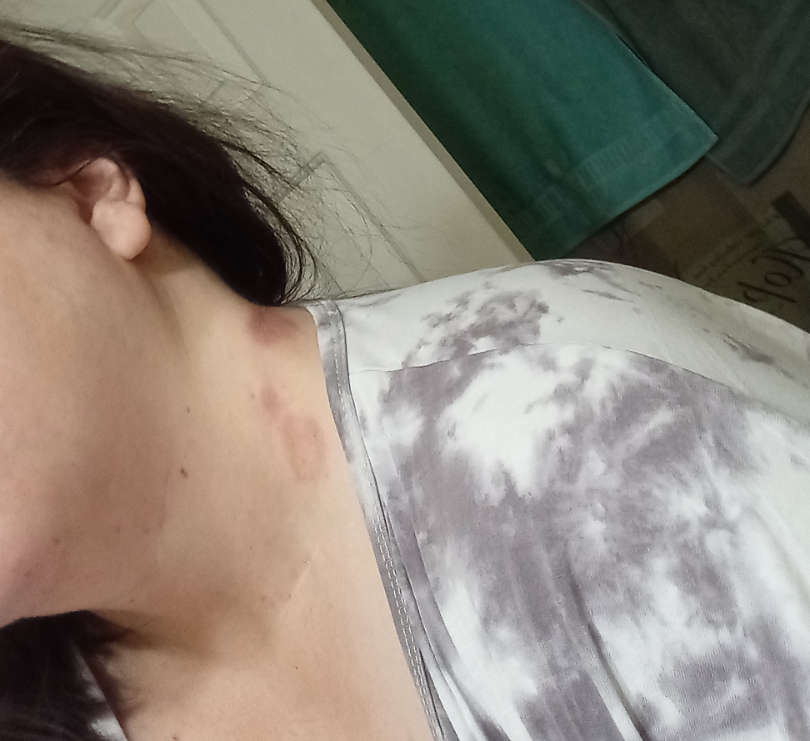assessment — indeterminate from the photograph